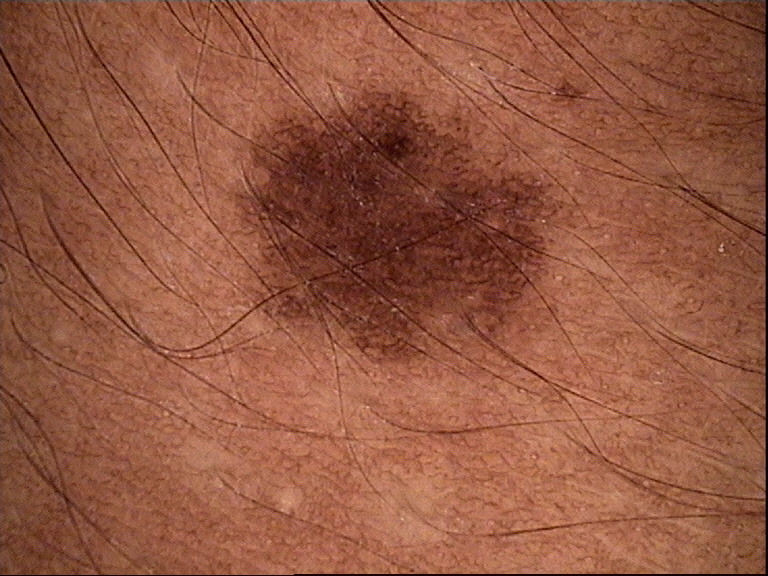Consistent with a dysplastic junctional nevus.